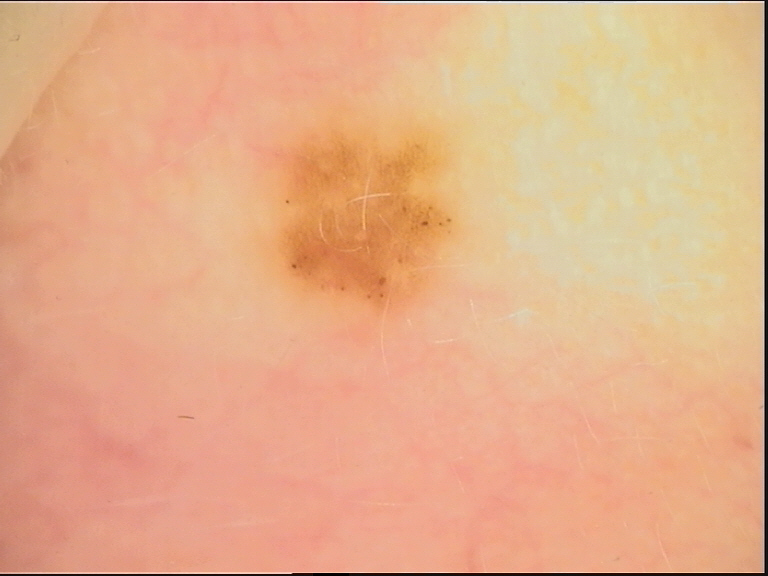Diagnosed as a dysplastic junctional nevus.